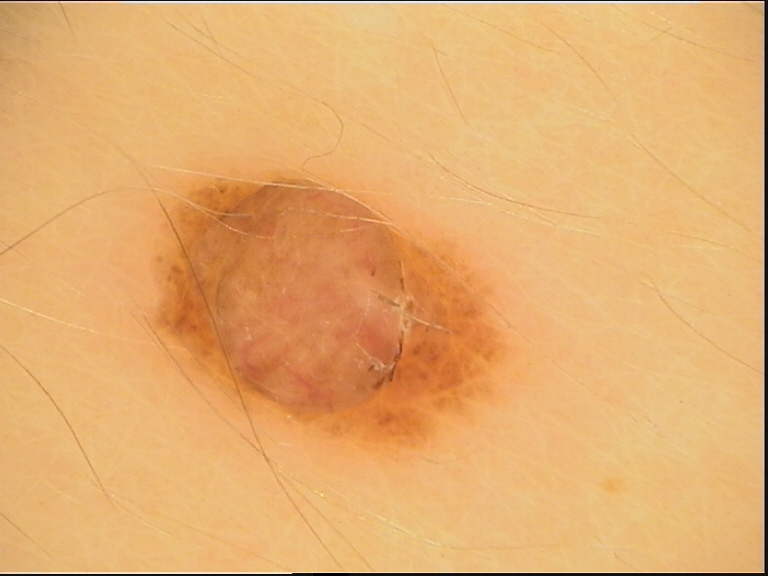Findings:
• imaging · dermatoscopy
• lesion type · banal
• label · dermal nevus (expert consensus)